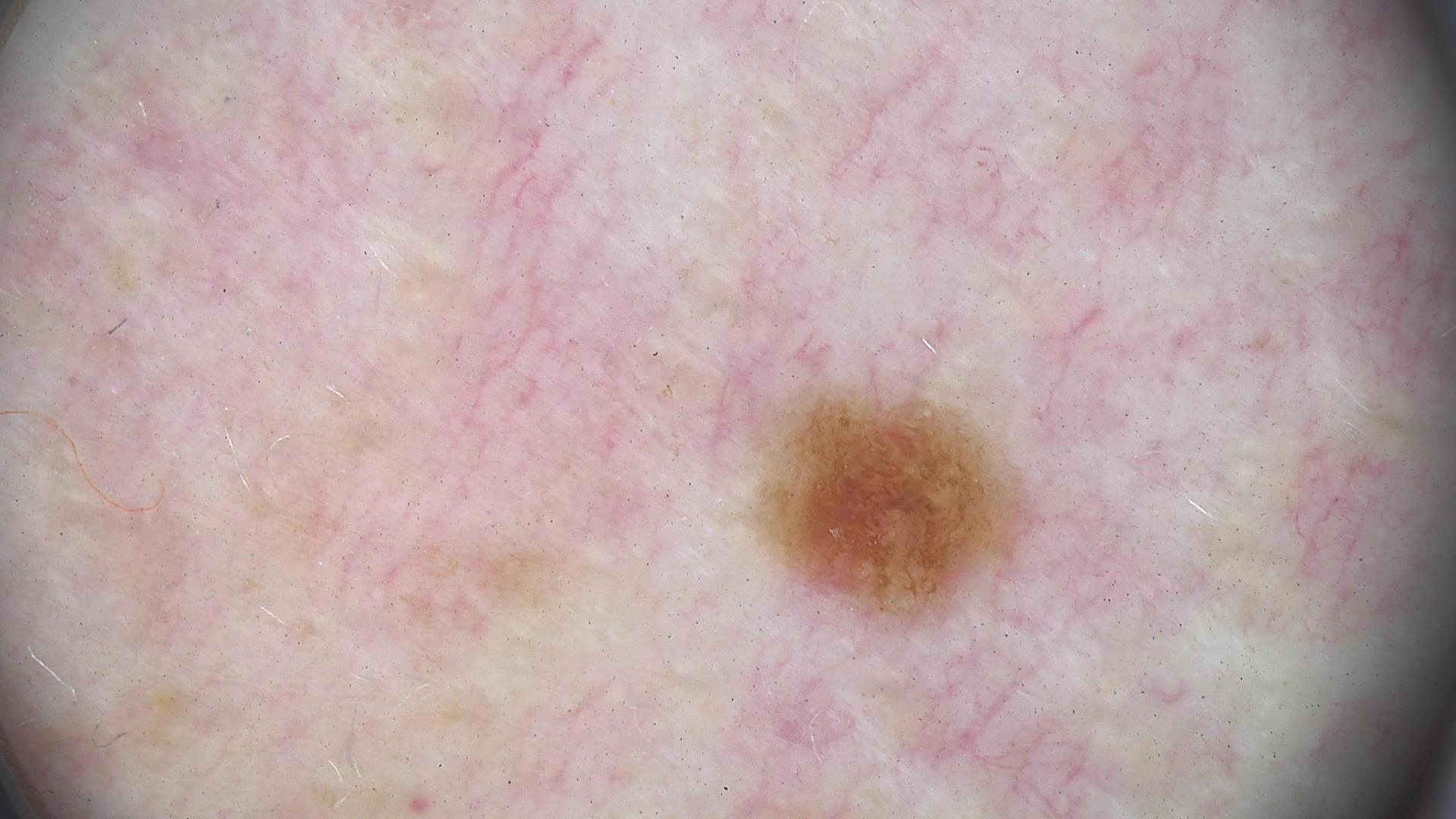A dermatoscopic image of a skin lesion. Classified as a dysplastic junctional nevus.